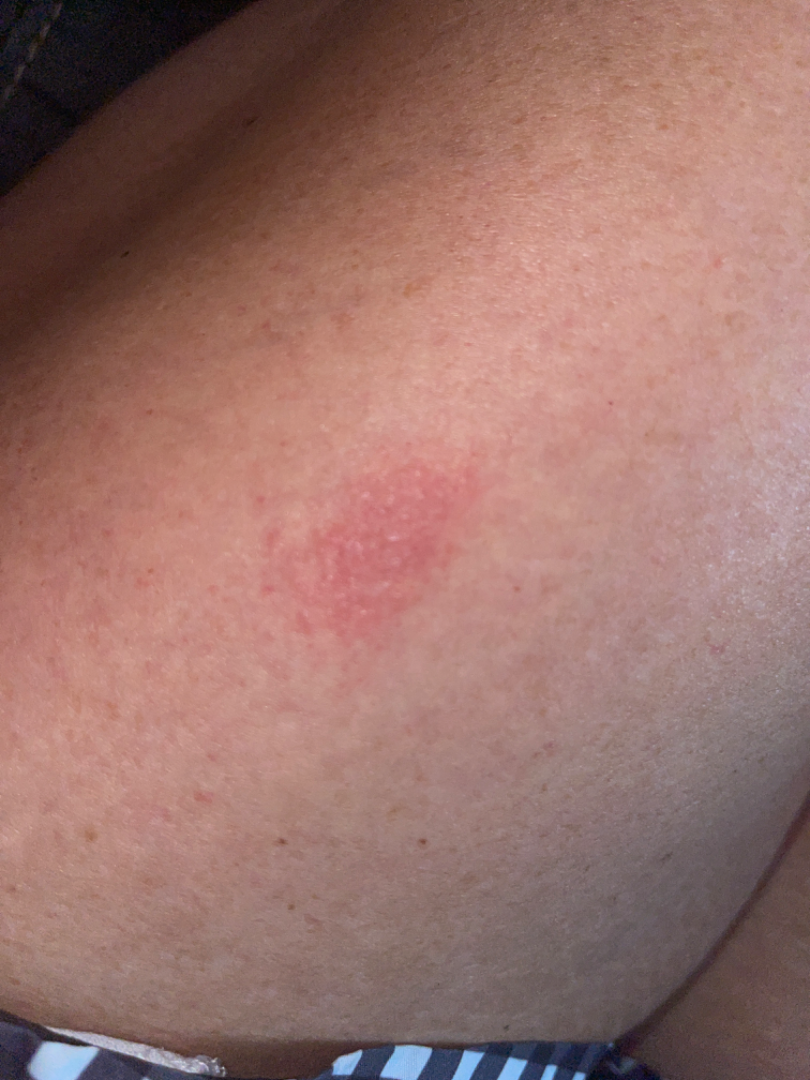• framing: close-up
• anatomic site: leg and arm
• differential diagnosis: most likely Eczema